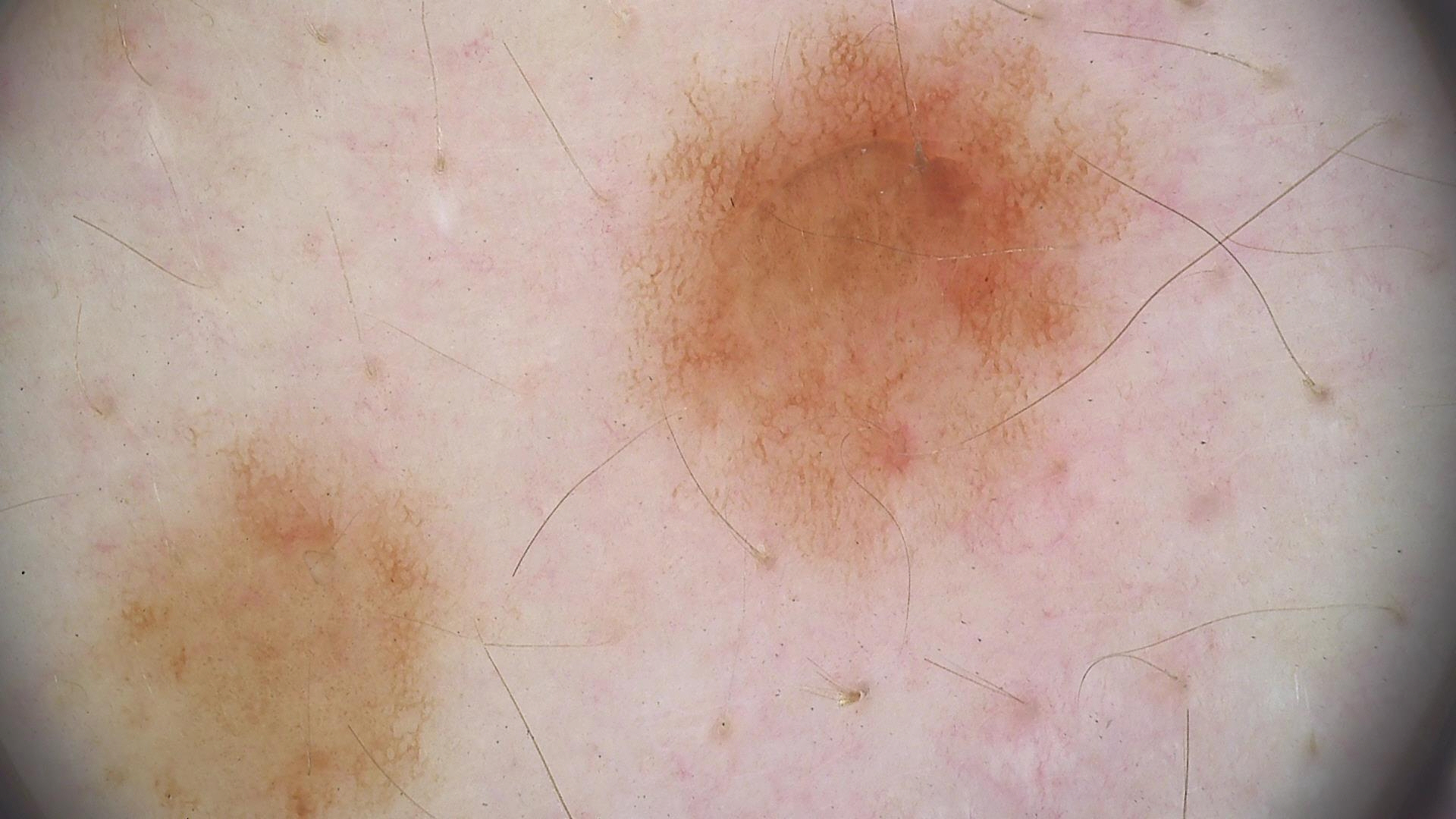imaging: dermoscopy | diagnostic label: dysplastic junctional nevus (expert consensus).